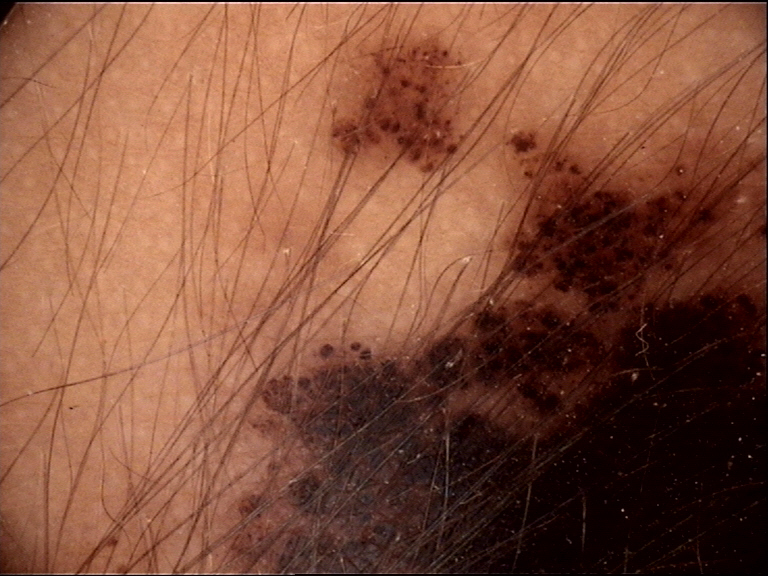Findings:
* image — dermoscopy
* class — congenital compound nevus (expert consensus)